A dermoscopic close-up of a skin lesion · the subject is a female aged approximately 30.
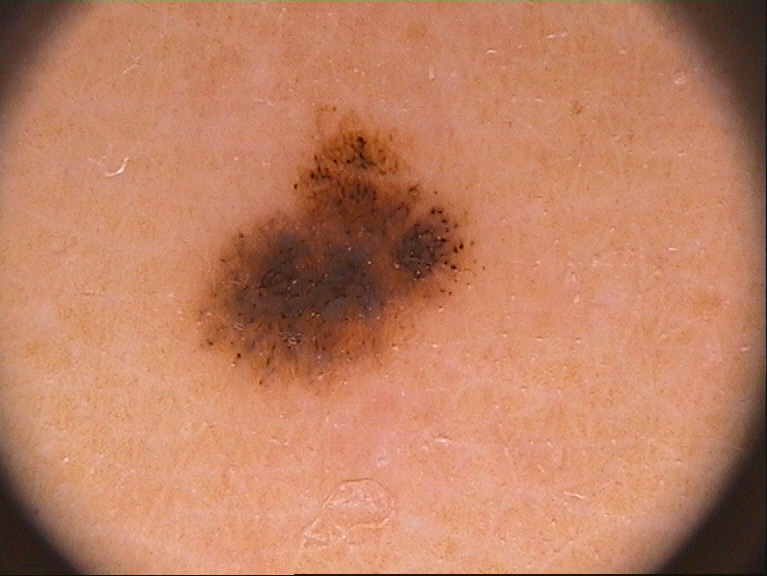extent = ~14% of the field
dermoscopic pattern = pigment network and globules; absent: milia-like cysts, negative network, and streaks
lesion location = bbox=[189, 103, 490, 401]
diagnosis = a melanocytic nevus